A dermoscopy image of a single skin lesion.
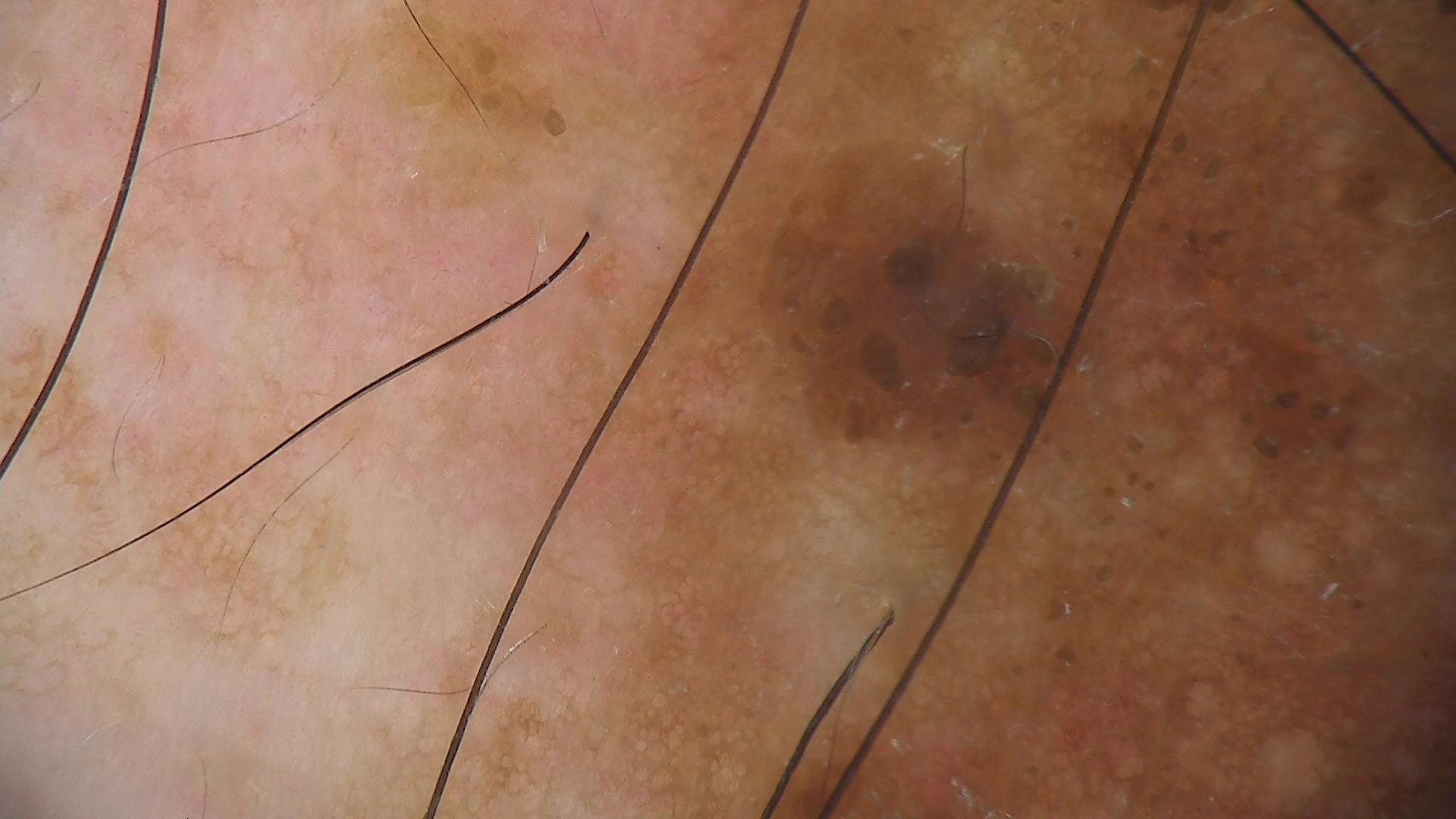This is a keratinocytic lesion.
The diagnostic label was a seborrheic keratosis.